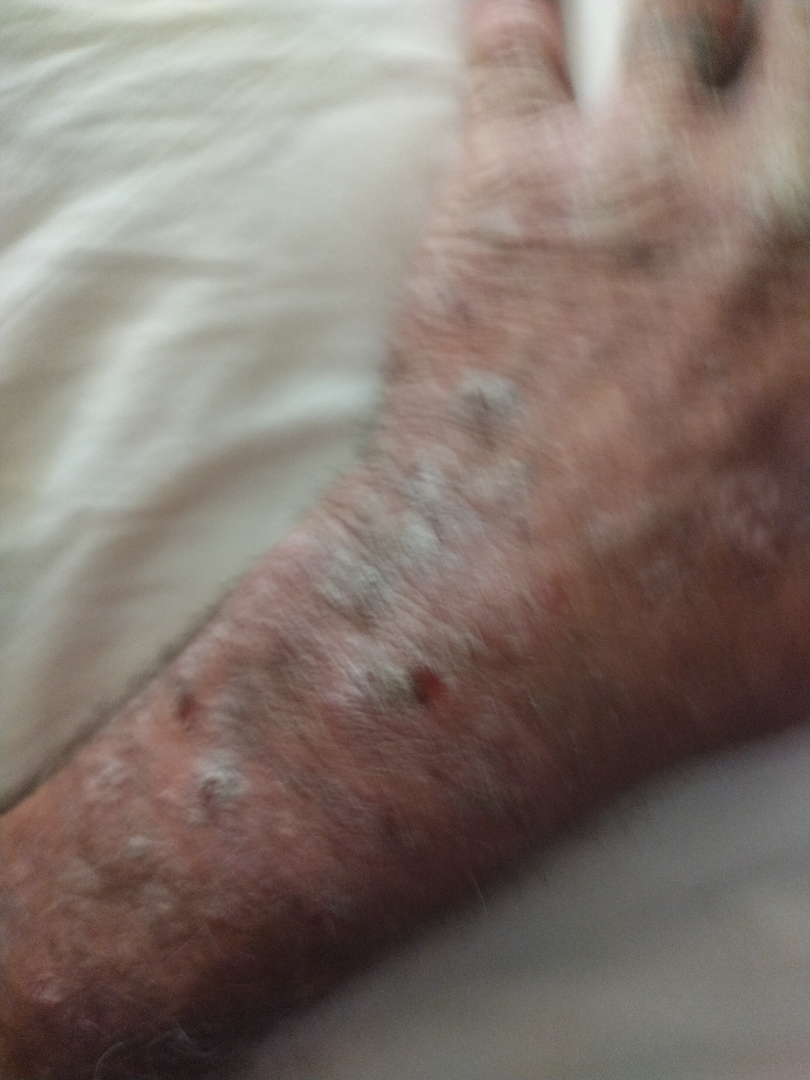Clinical context:
Located on the arm. Self-categorized by the patient as a rash. Texture is reported as rough or flaky and raised or bumpy. Reported duration is more than one year. Fitzpatrick phototype III. The contributor is 50–59, male. This image was taken at a distance.
Assessment:
On remote review of the image, Prurigo nodularis and Actinic Keratosis were each considered, in no particular order.